A skin lesion imaged with a dermatoscope, the patient is a male in their mid-60s — 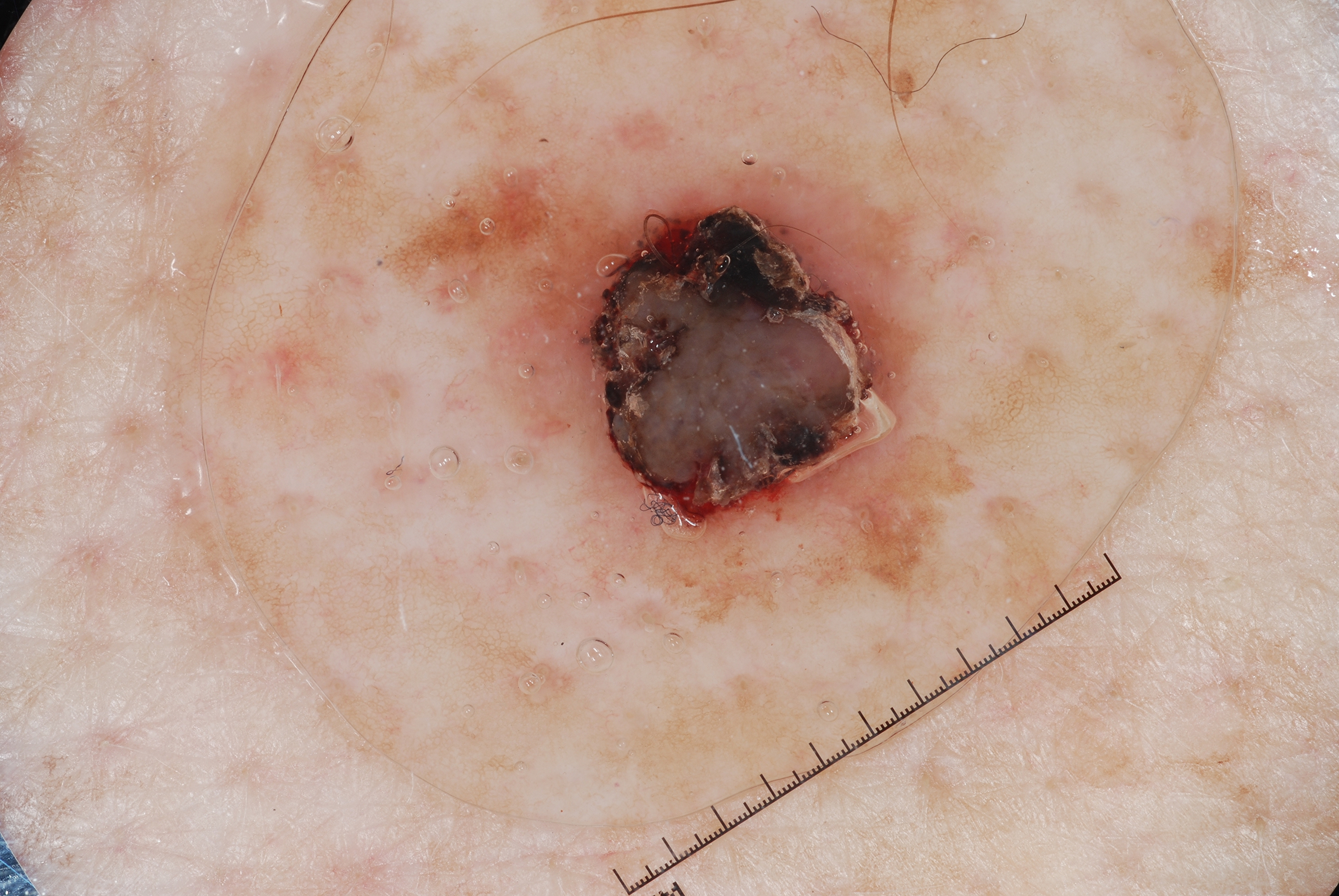Findings:
The dermoscopic pattern shows milia-like cysts, with no streaks, pigment network, or negative network. In (x1, y1, x2, y2) order, lesion location: [391,91,981,659]. The lesion takes up a moderate portion of the field.
Impression:
Consistent with a seborrheic keratosis.